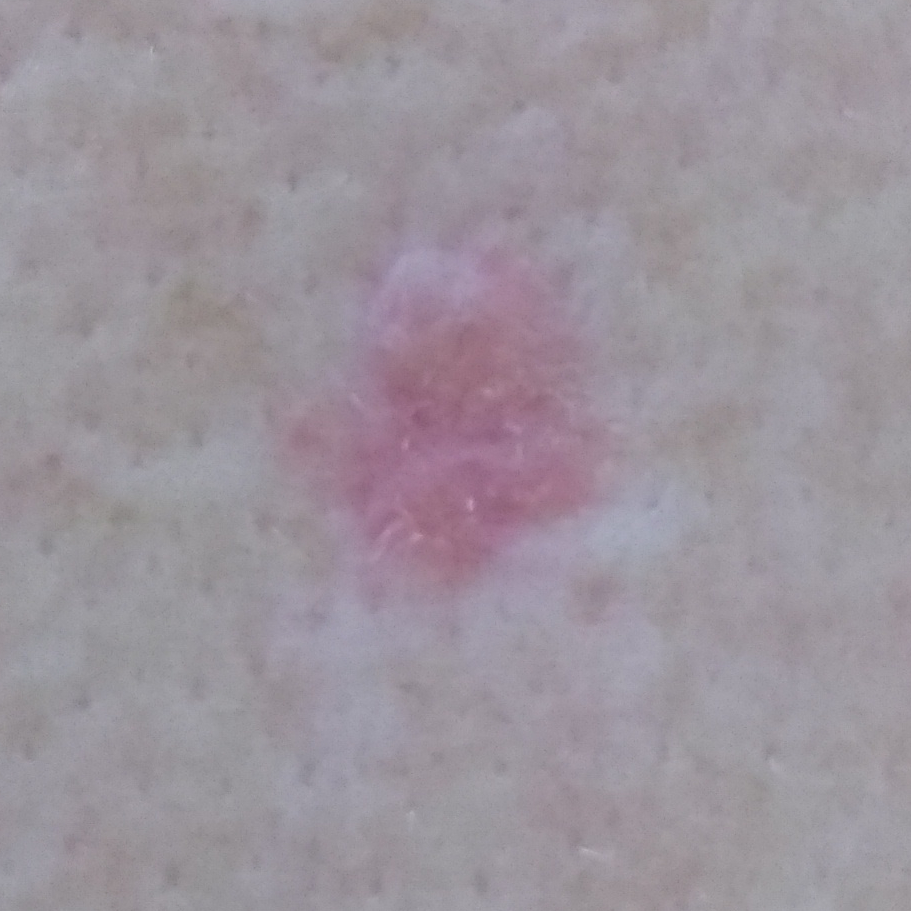A male patient aged 57. The lesion is located on the back. On biopsy, the diagnosis was a basal cell carcinoma.